This is a close-up image. The affected area is the head or neck: 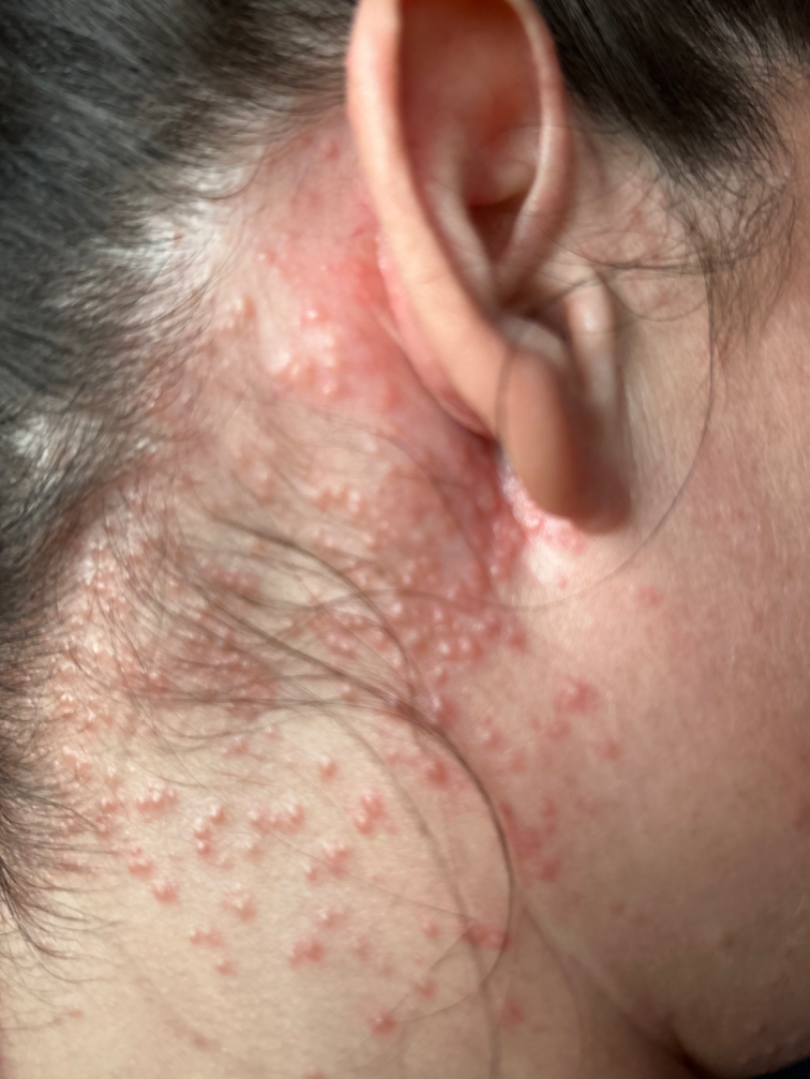assessment = unable to determine.